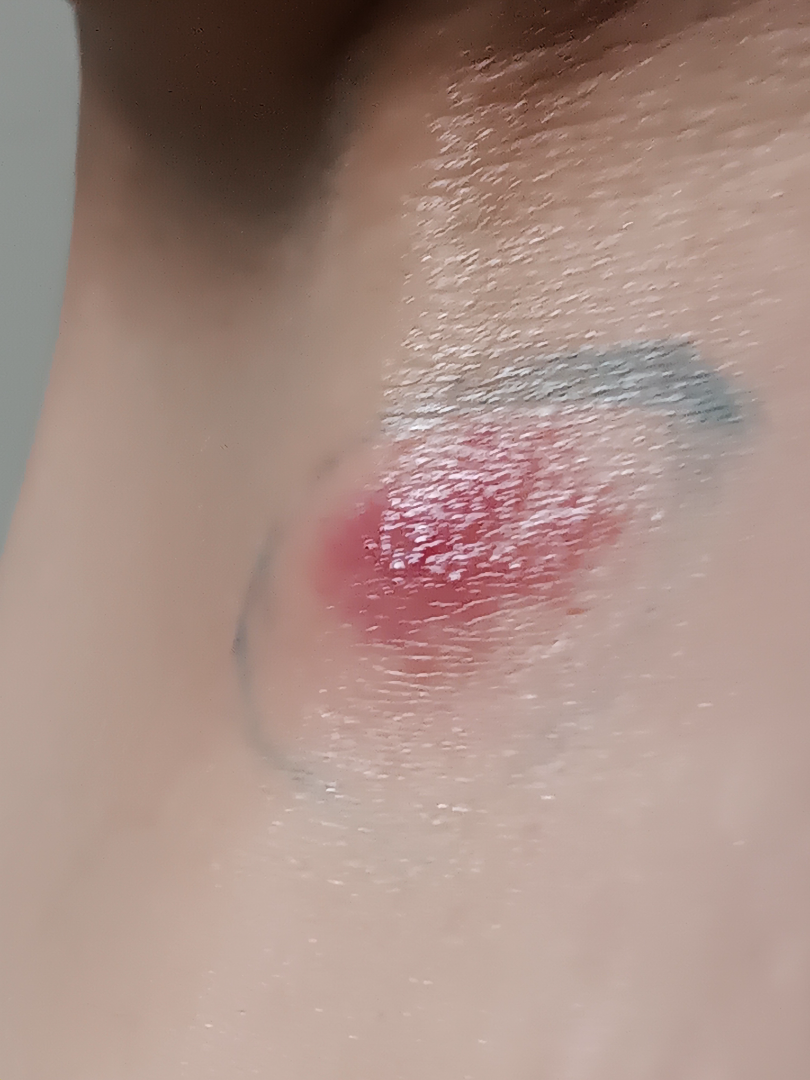Review:
The differential is split between Abscess and Insect Bite; less likely is B-Cell Cutaneous Lymphoma.